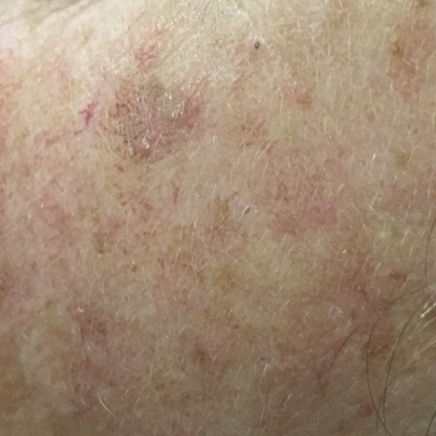| field | value |
|---|---|
| modality | clinical photo |
| patient | aged 45 |
| site | the face |
| symptoms | itching, growth |
| diagnosis | actinic keratosis (clinical consensus) |